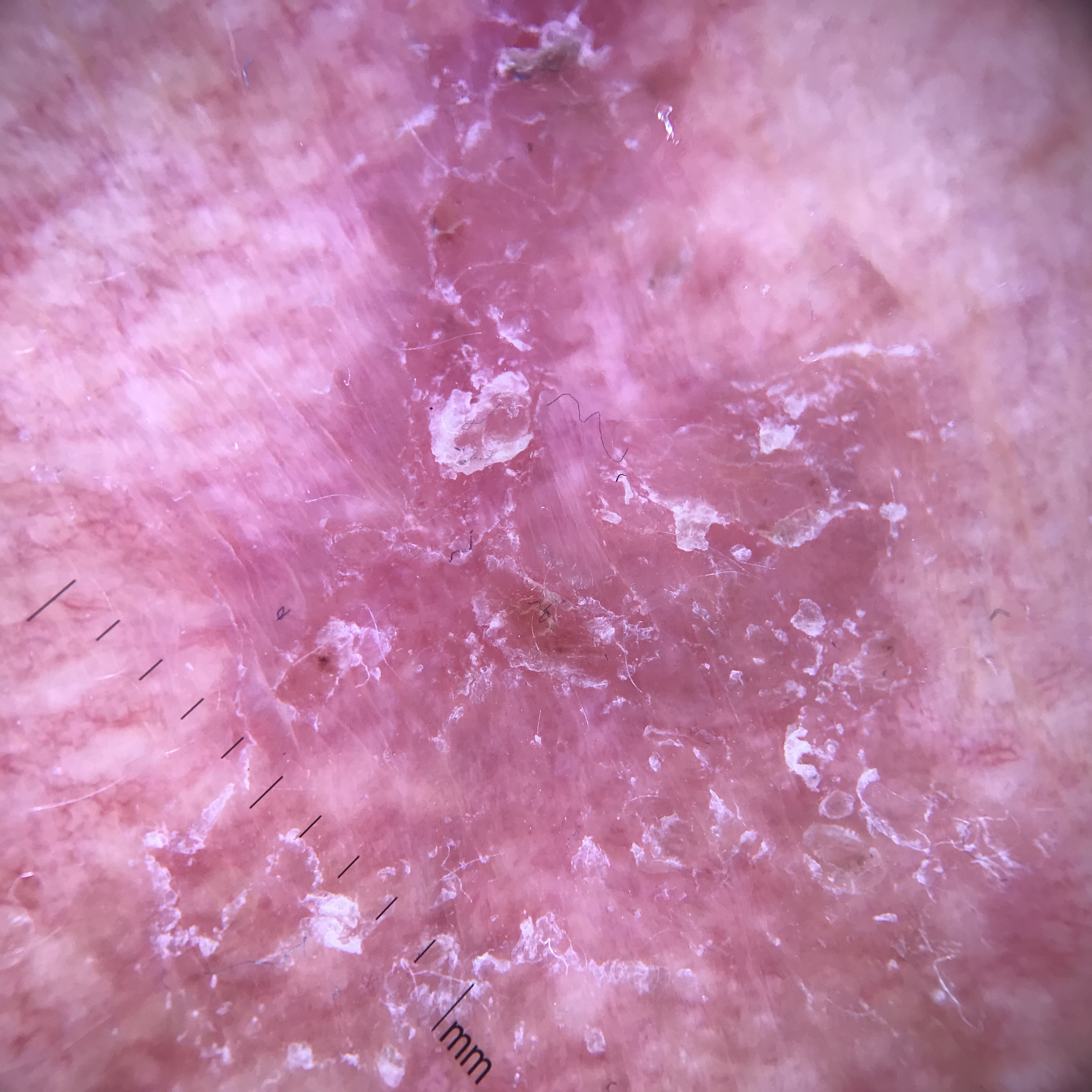Pathology: The biopsy diagnosis was Bowen's disease.